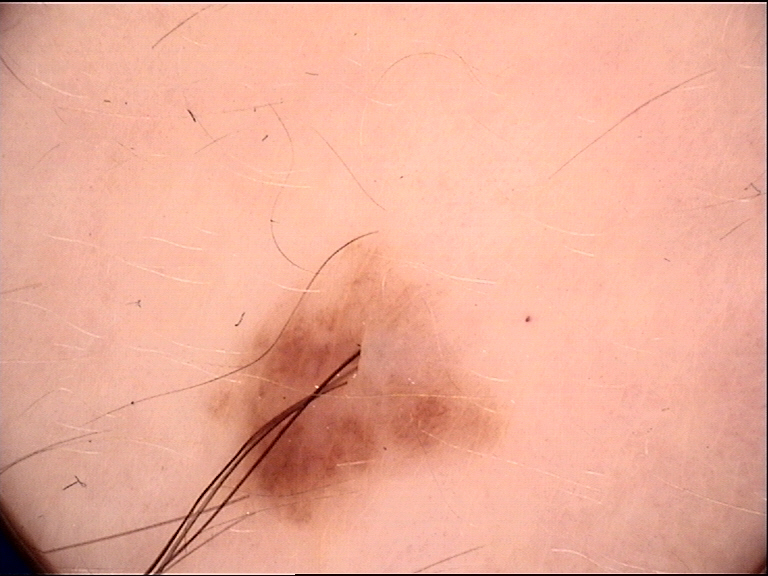Q: What is the imaging modality?
A: dermoscopy
Q: What is this lesion?
A: dysplastic compound nevus (expert consensus)